Dermoscopy of a skin lesion:
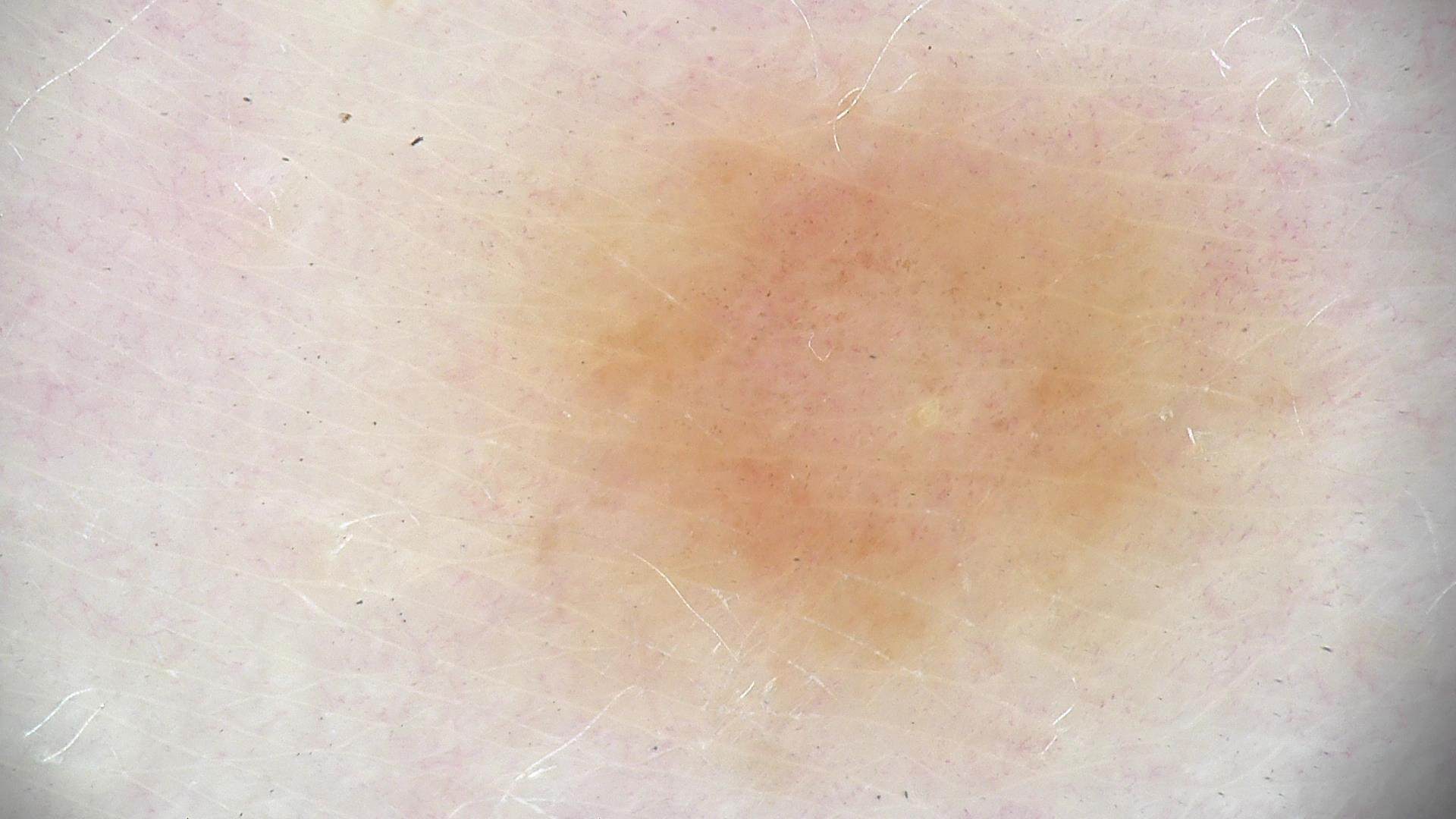Case:
– diagnostic label · dysplastic junctional nevus (expert consensus)